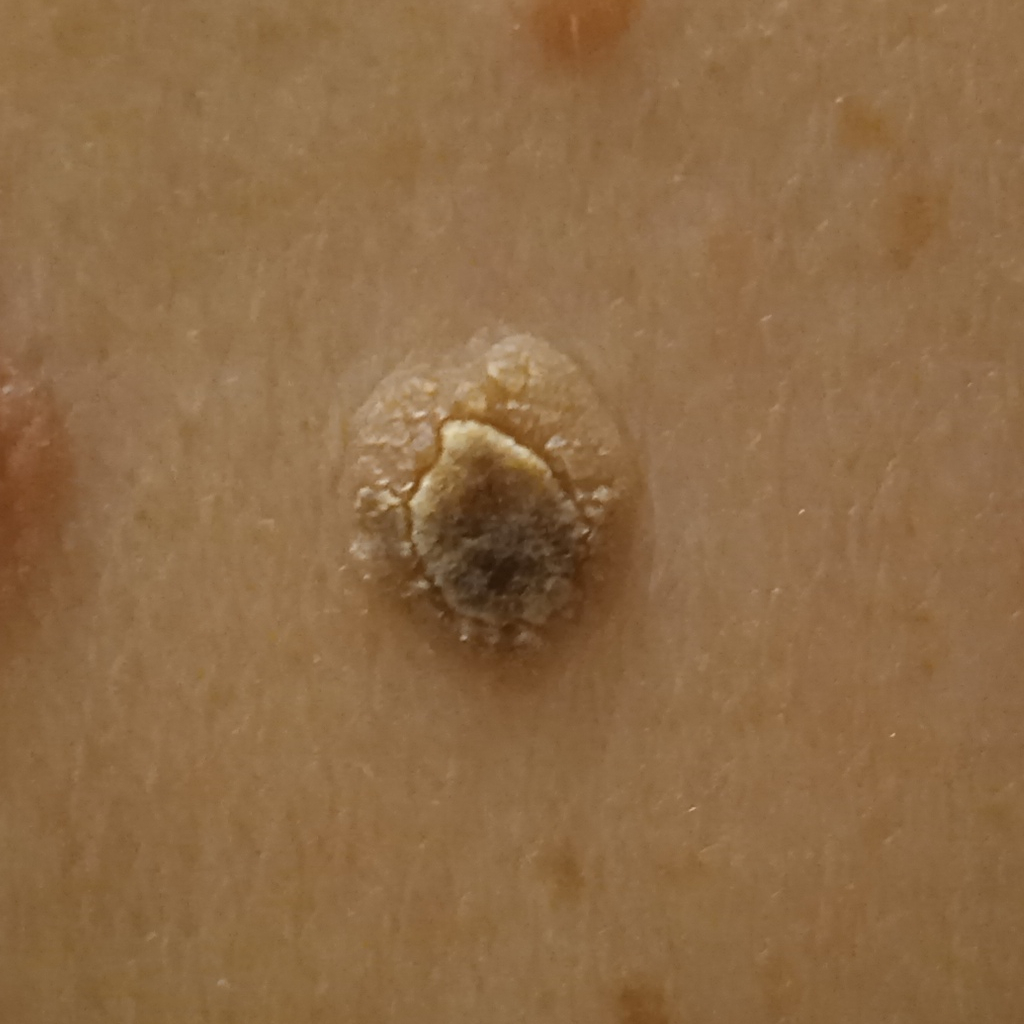image type: clinical photograph
nevus count: a moderate number of melanocytic nevi
clinical context: research study (no referral diagnosis)
sun reaction: skin reddens painfully with sun exposure
subject: female, aged 81
site: the back
diagnosis: seborrheic keratosis (dermatologist consensus)